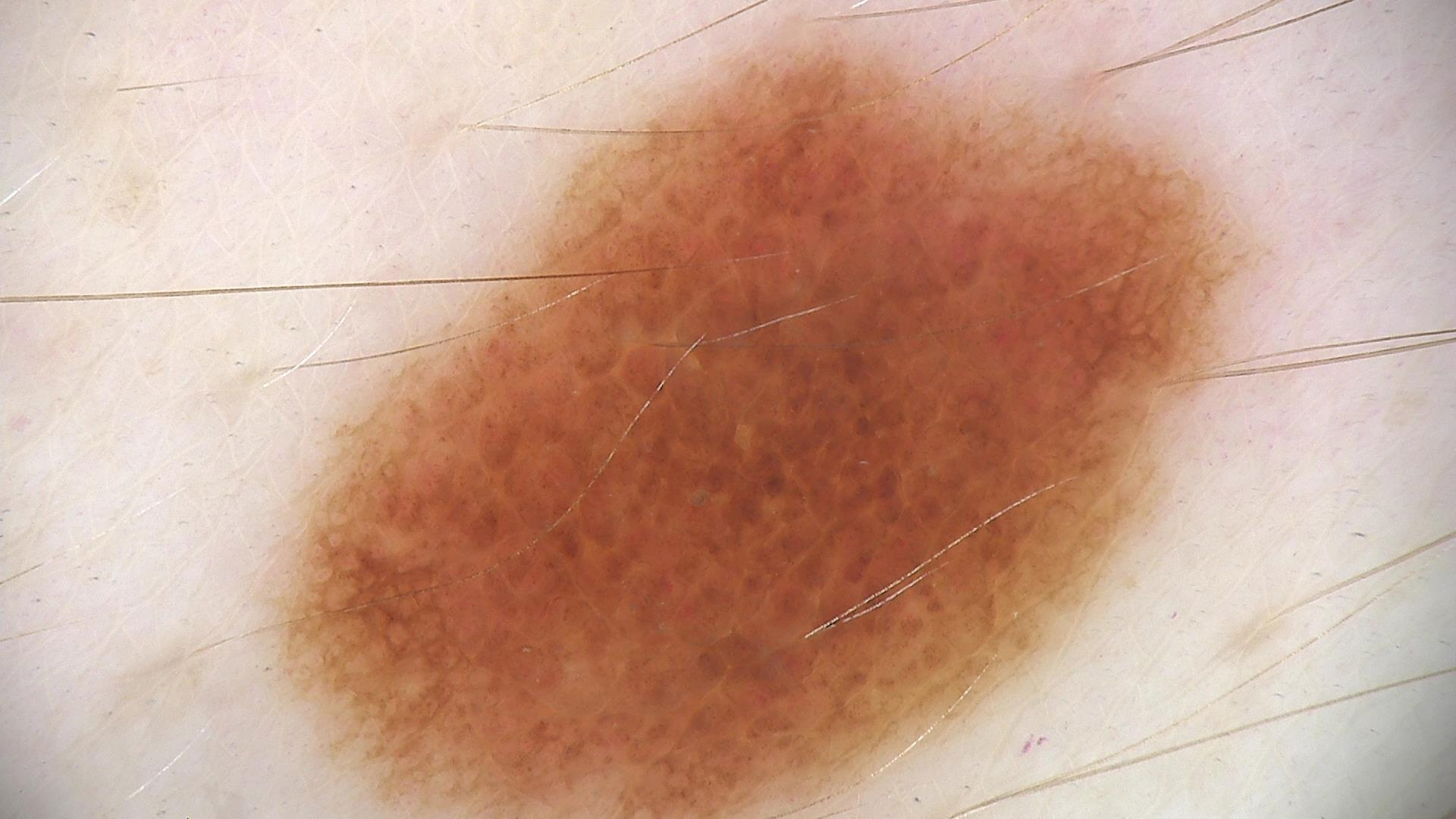| feature | finding |
|---|---|
| image | dermoscopy |
| assessment | dysplastic junctional nevus (expert consensus) |